A close-up photograph:
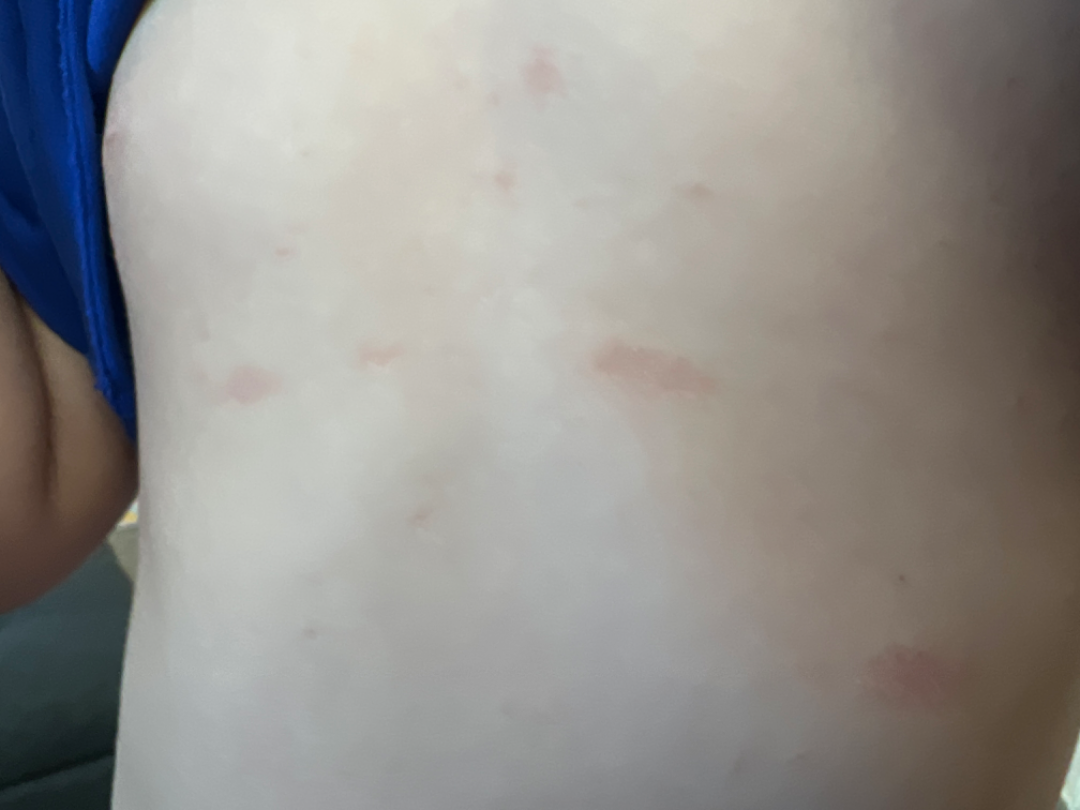Findings:
The primary impression is Pityriasis rosea.